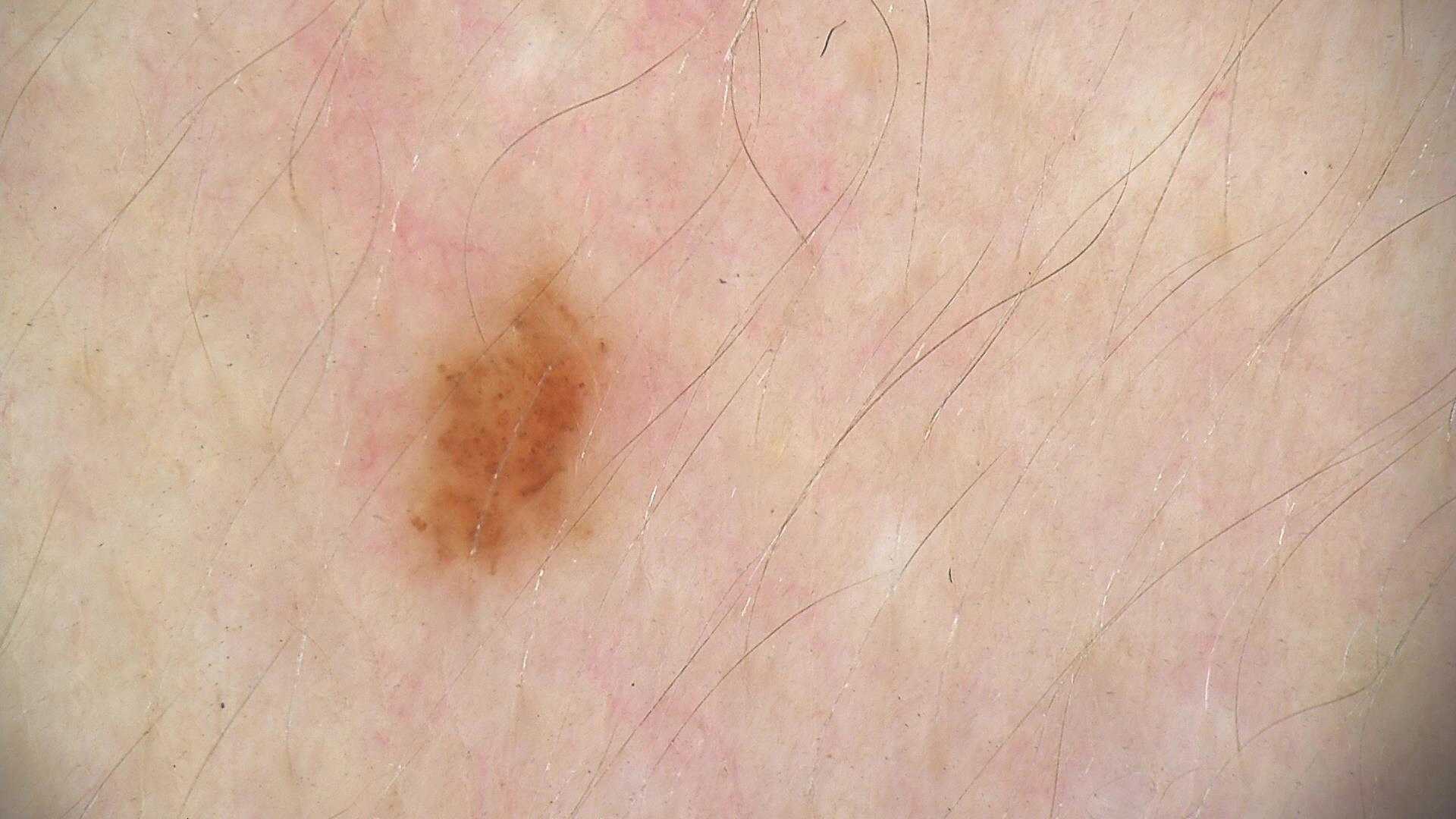diagnosis:
  name: dysplastic junctional nevus
  code: jd
  malignancy: benign
  super_class: melanocytic
  confirmation: expert consensus